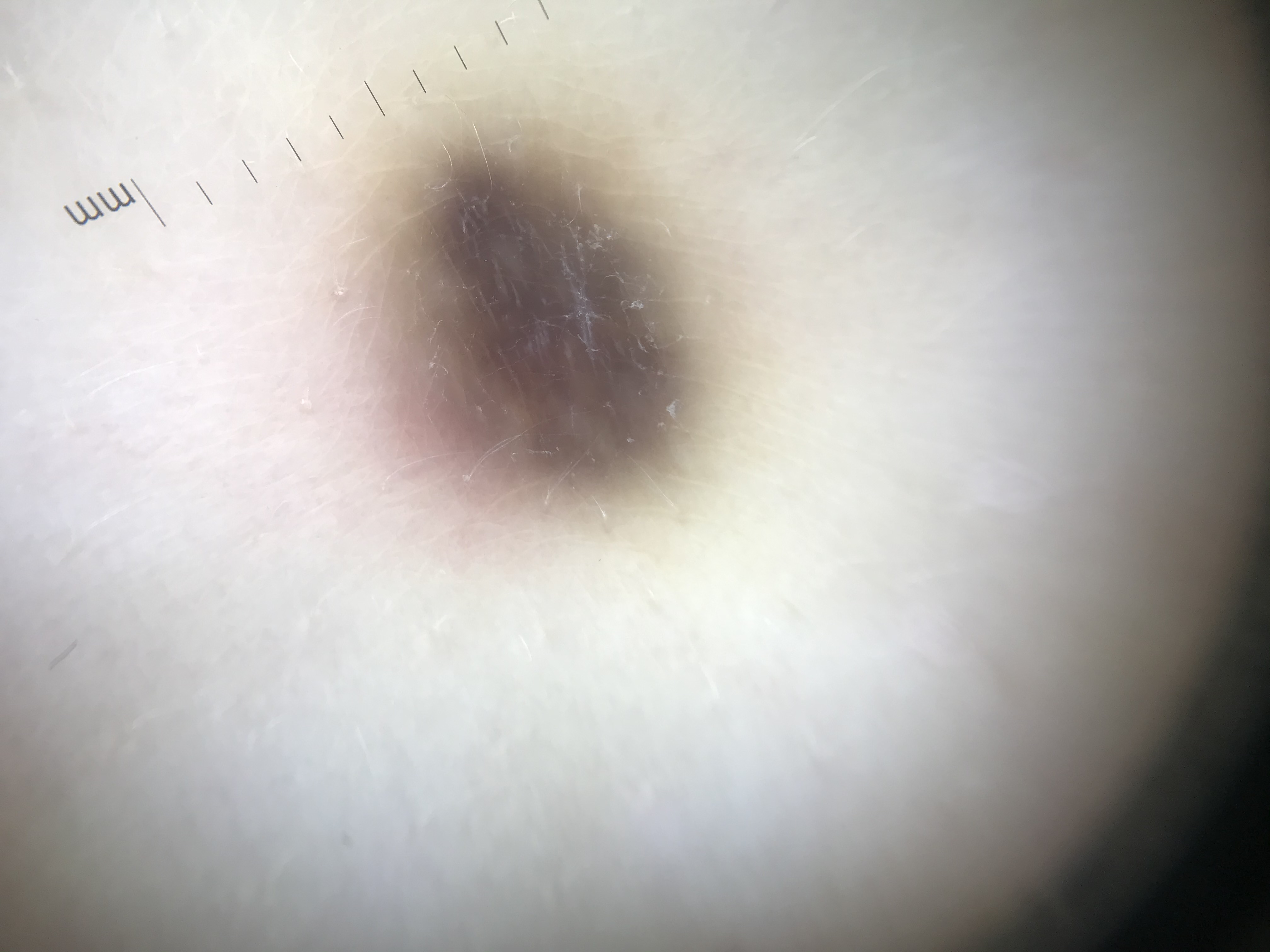imaging: dermoscopy; class: blue nevus (expert consensus).